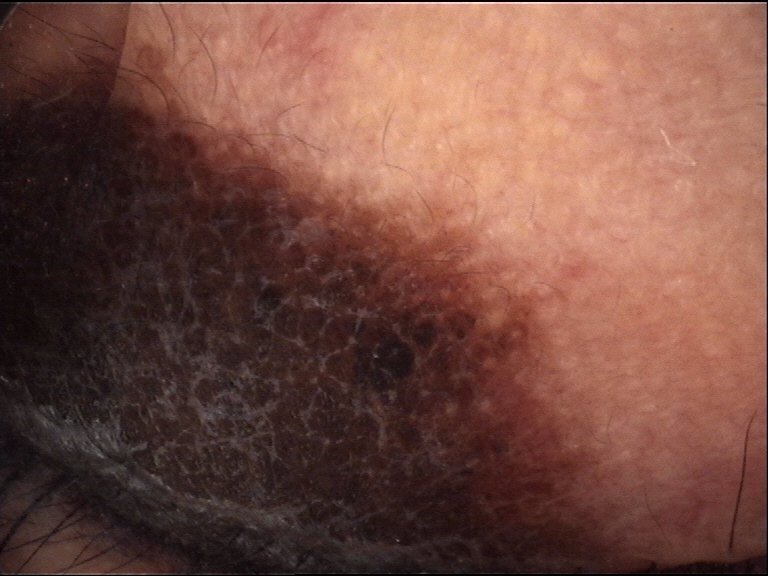diagnosis:
  name: congenital compound nevus
  code: ccb
  malignancy: benign
  super_class: melanocytic
  confirmation: expert consensus